Dermoscopy of a skin lesion:
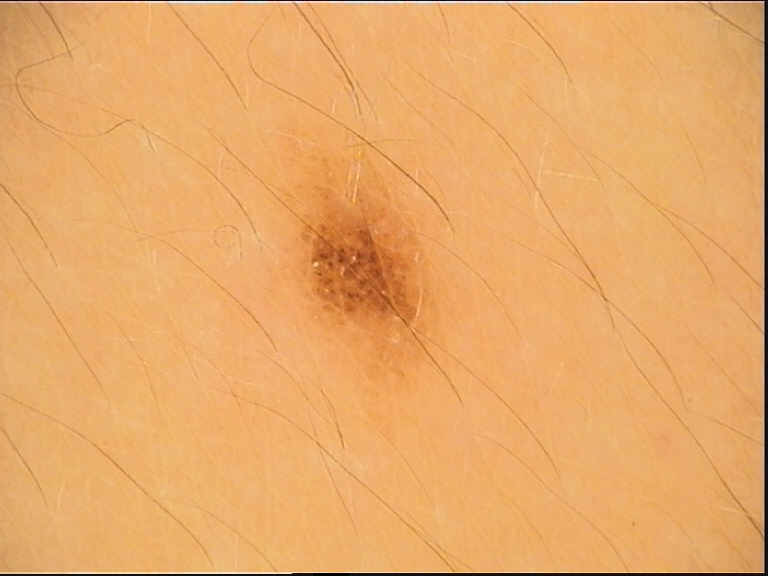Impression:
Labeled as a dysplastic junctional nevus.